A skin lesion imaged with contact-polarized dermoscopy — 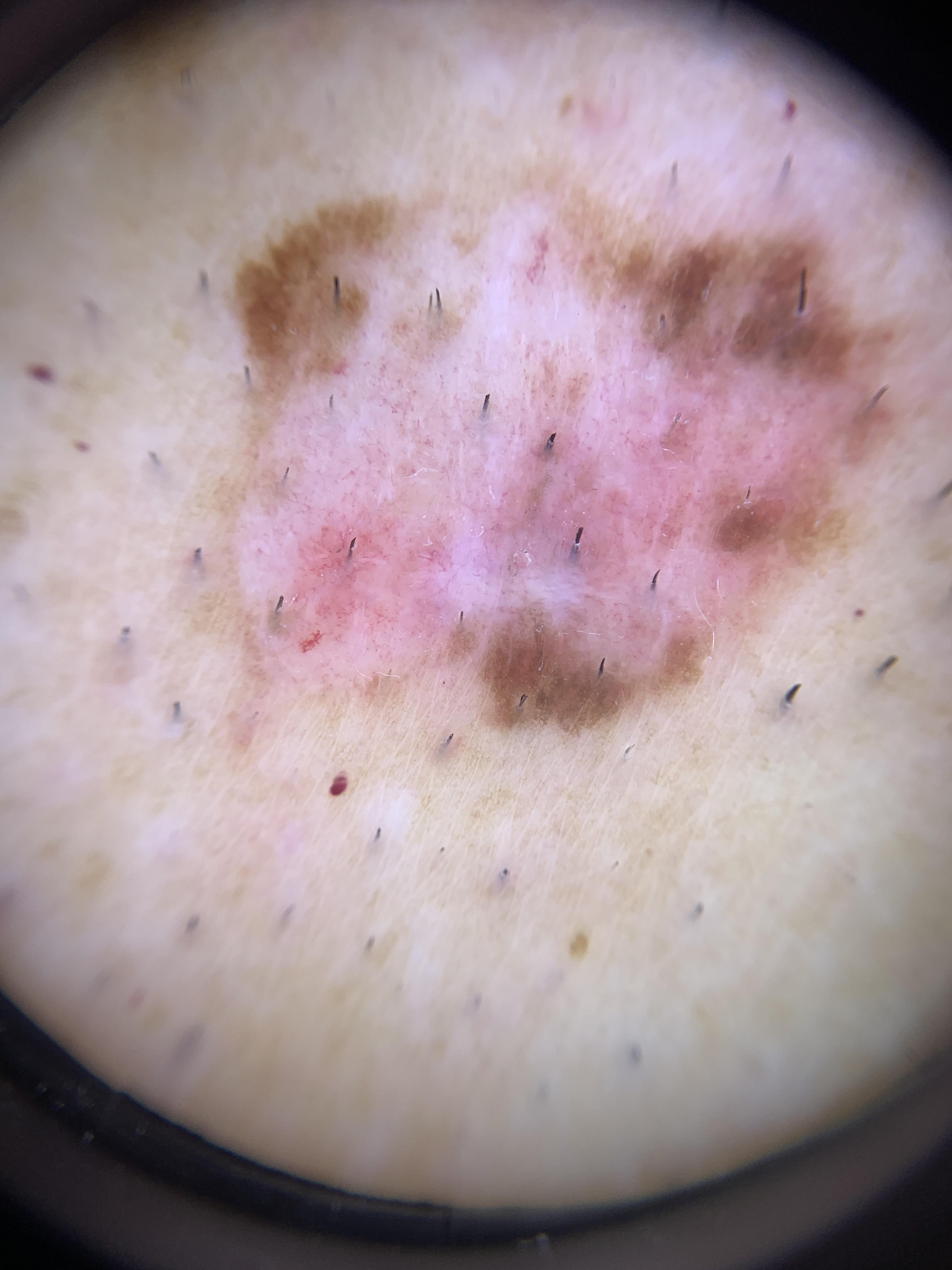The lesion is located on the trunk. On biopsy, the diagnosis was a skin cancer — a melanoma.